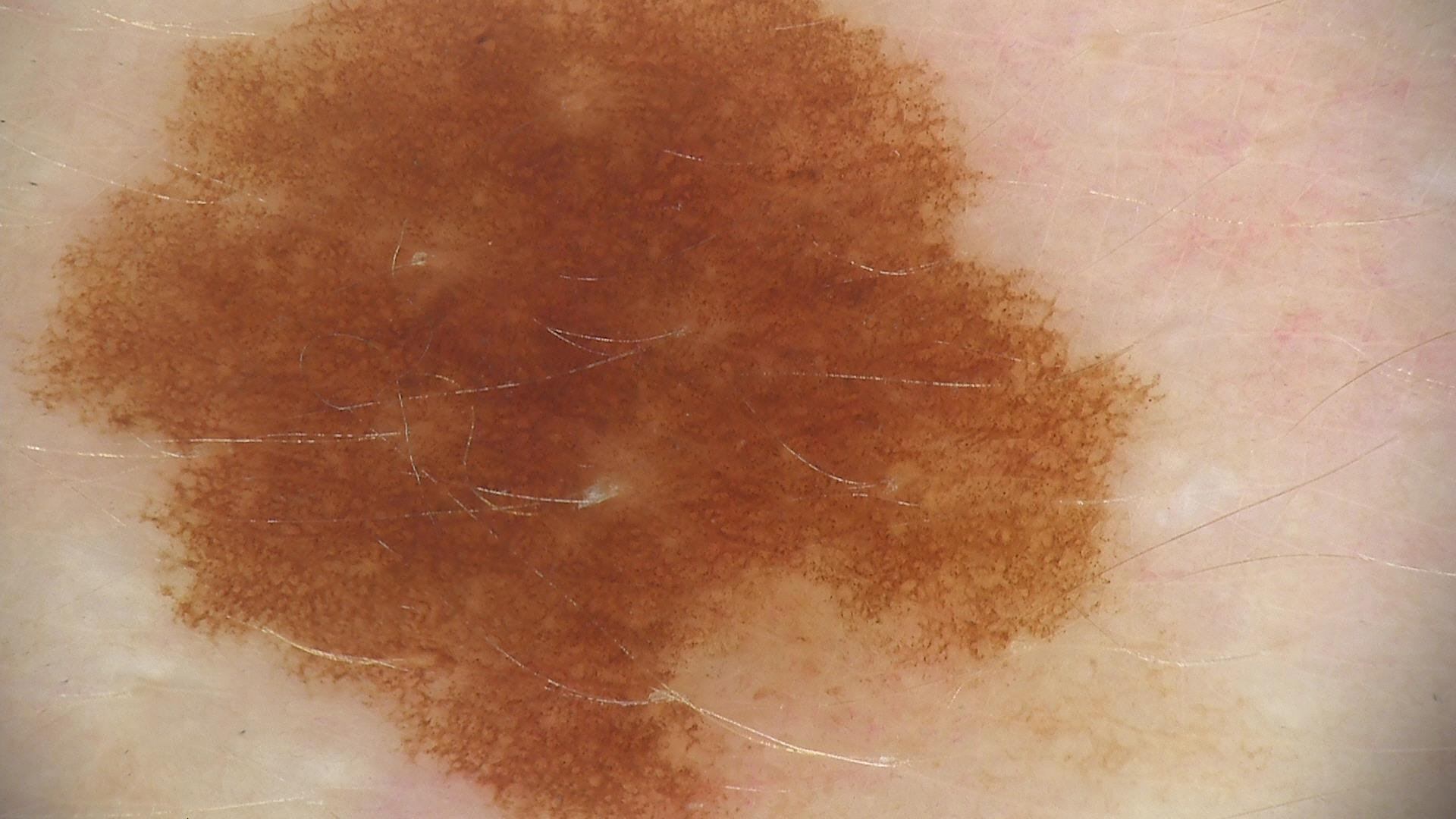Dermoscopy of a skin lesion. Diagnosed as a benign lesion — a dysplastic junctional nevus.